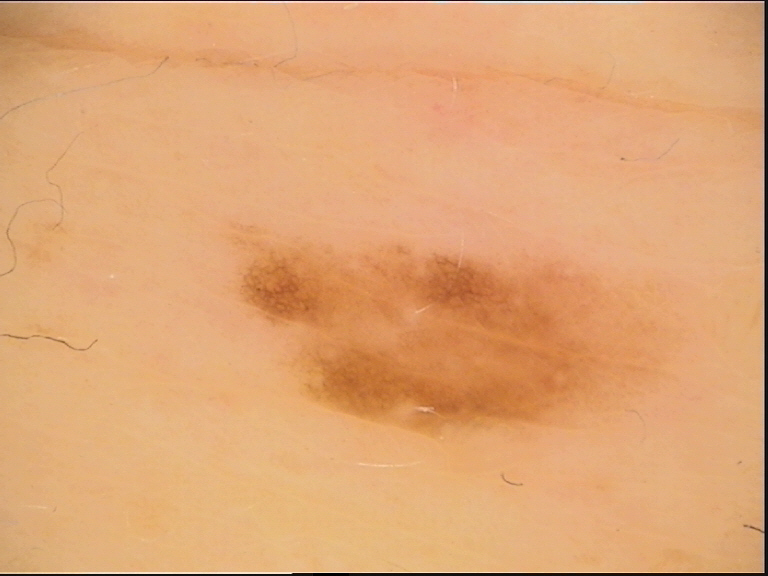Q: What is the imaging modality?
A: dermoscopy
Q: What was the diagnostic impression?
A: dysplastic junctional nevus (expert consensus)